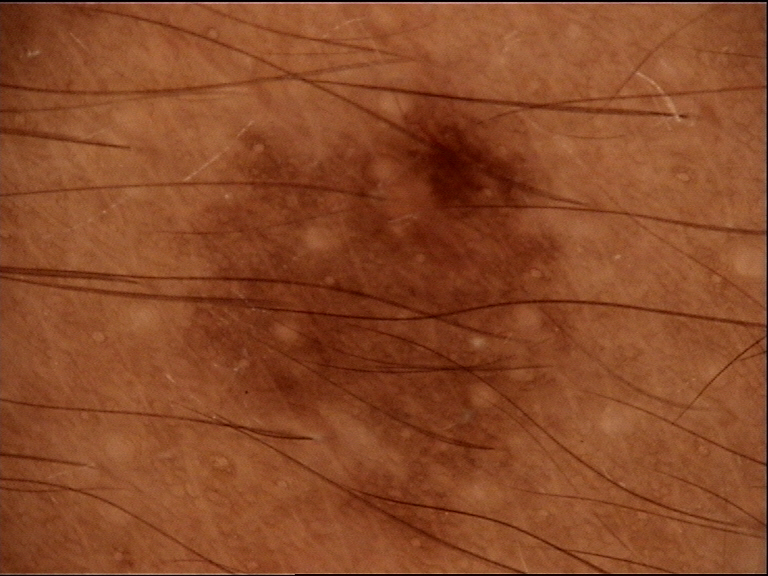{
  "diagnosis": {
    "name": "dysplastic junctional nevus",
    "code": "jd",
    "malignancy": "benign",
    "super_class": "melanocytic",
    "confirmation": "expert consensus"
  }
}